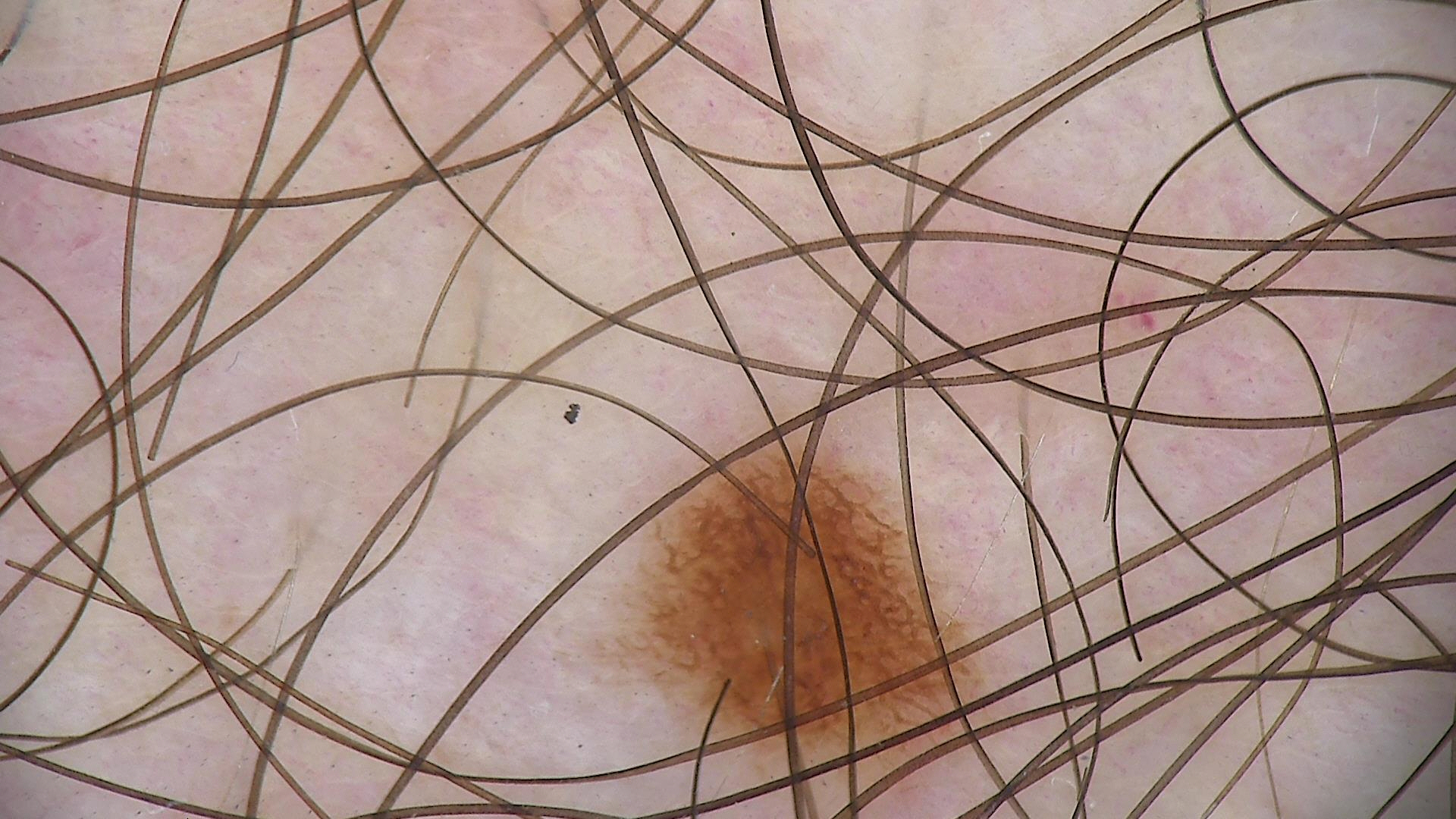image type: dermoscopy, class: junctional nevus (expert consensus).